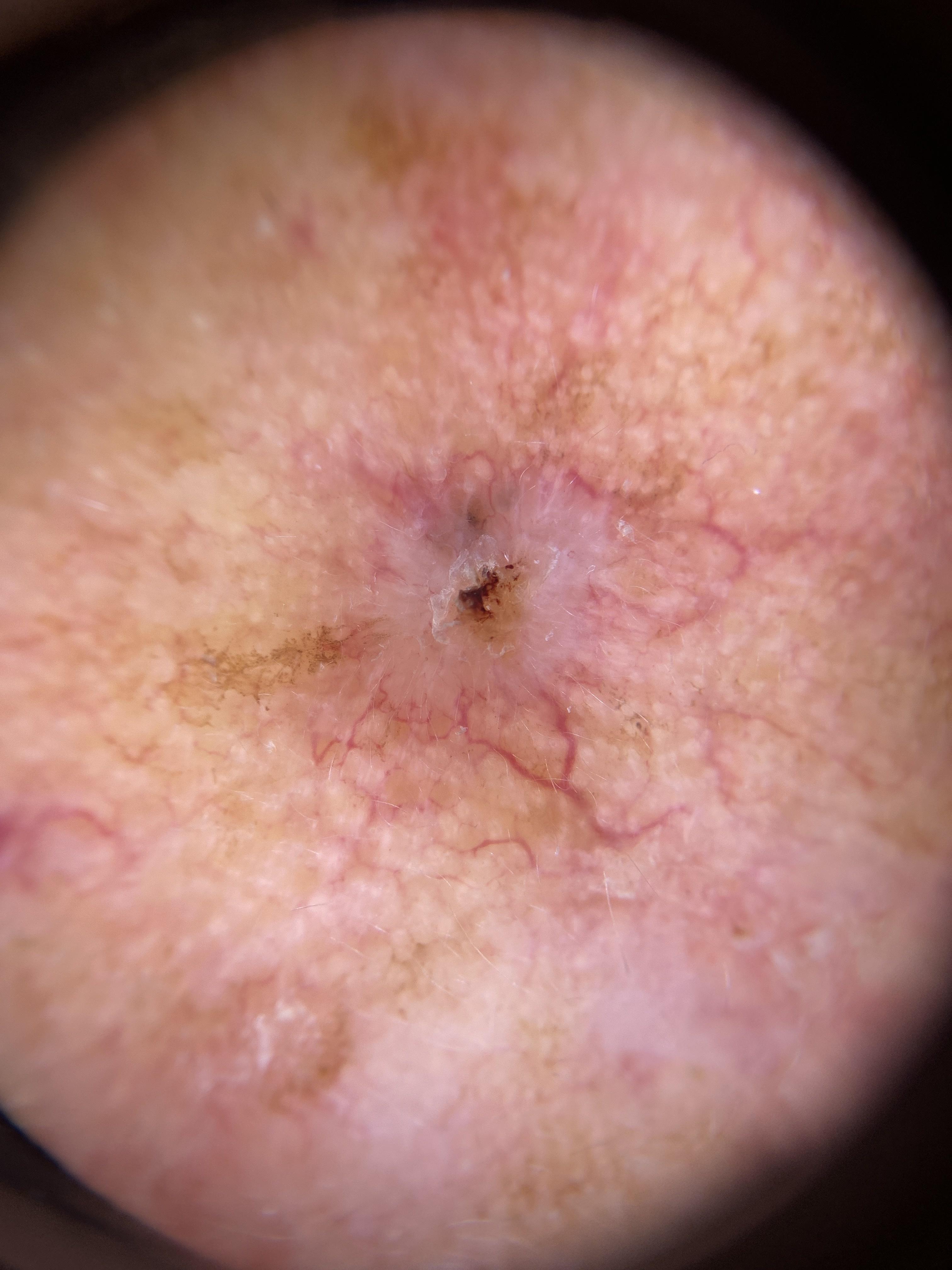The biopsy diagnosis was a basal cell carcinoma.